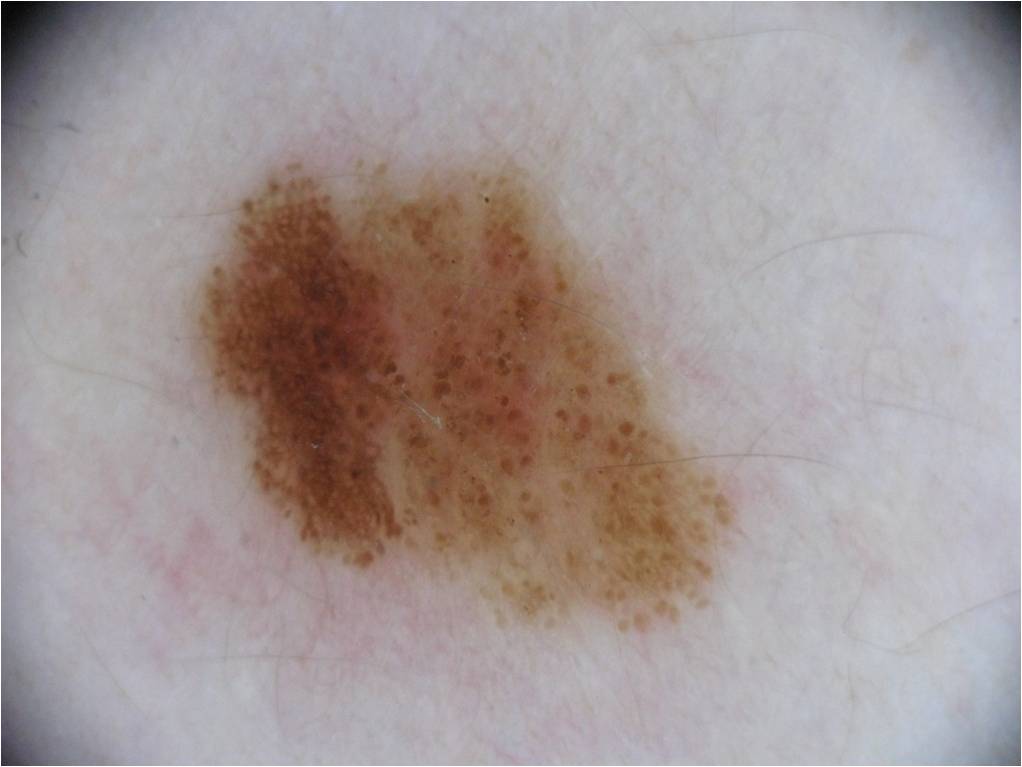image type — dermatoscopic image of a skin lesion | lesion bbox — 185 156 732 628 | diagnosis — a melanocytic nevus, a benign lesion.